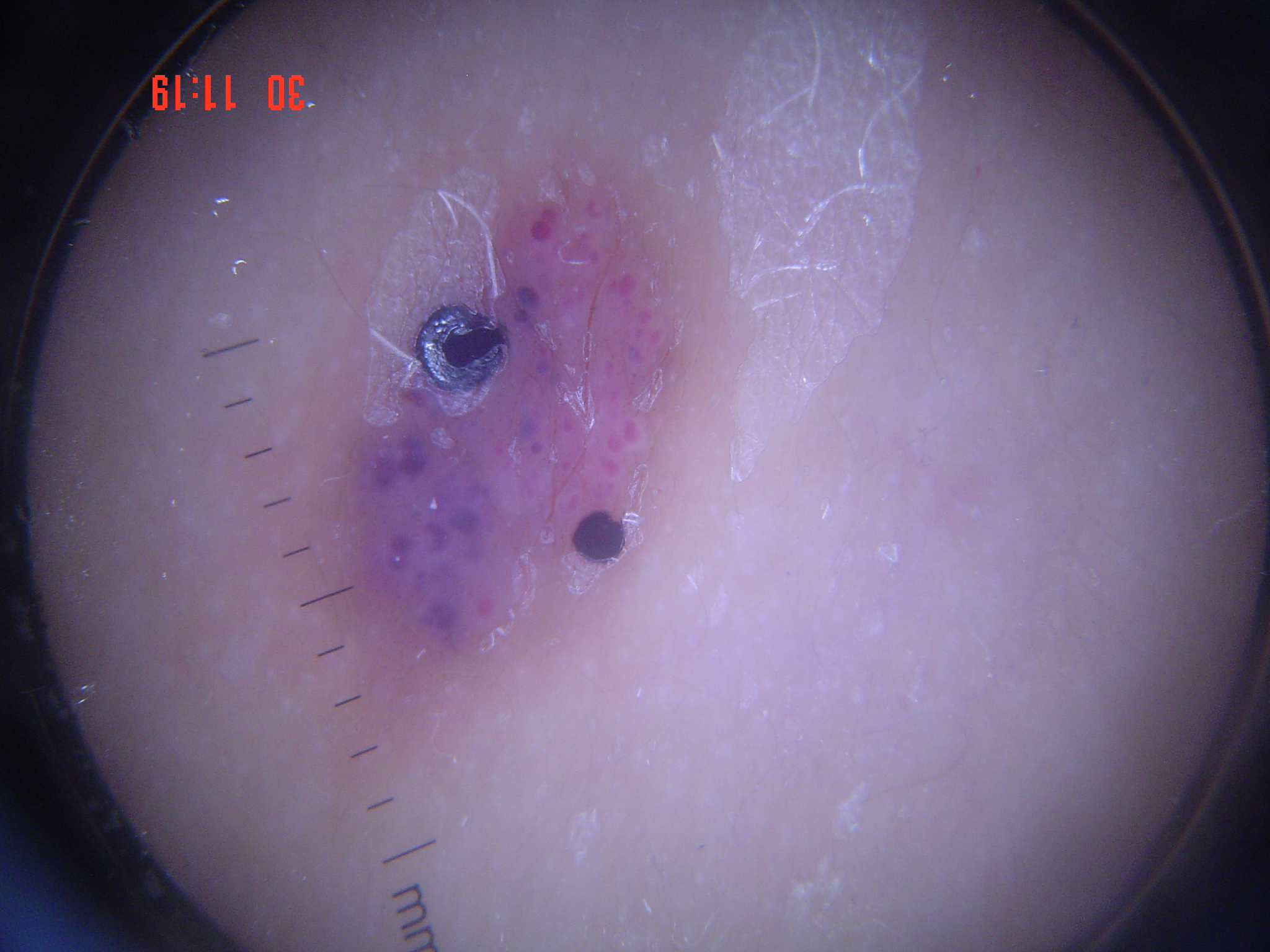{
  "diagnosis": {
    "name": "angiokeratoma",
    "code": "angk",
    "malignancy": "benign",
    "super_class": "non-melanocytic",
    "confirmation": "expert consensus"
  }
}